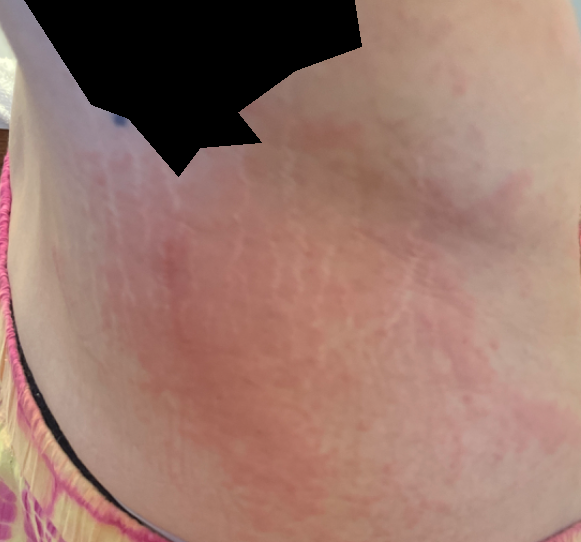Present for less than one week. Texture is reported as raised or bumpy. The arm, back of the torso and leg are involved. This image was taken at a distance. The patient considered this a rash. The patient notes itching. On dermatologist assessment of the image, Urticaria and Drug Rash were each considered, in no particular order; less likely is Leukocytoclastic Vasculitis.